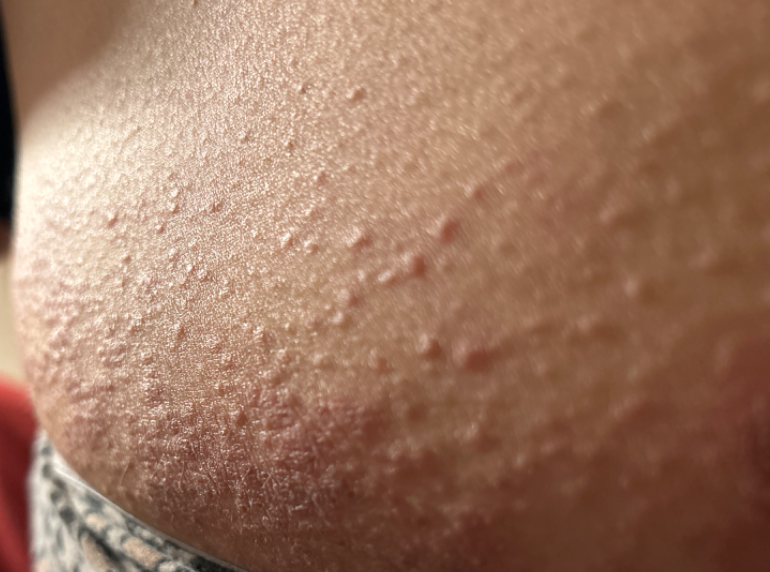| feature | finding |
|---|---|
| view | at an angle |
| affected area | leg, head or neck, front of the torso and back of the torso |
| differential | Eczema (1.00) |